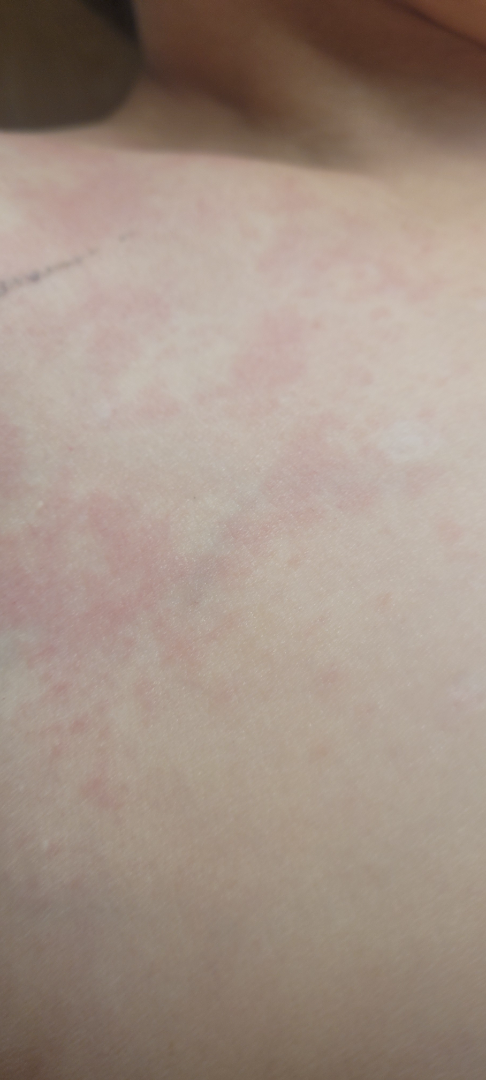assessment — indeterminate from the photograph; shot type — at an angle; anatomic site — head or neck and front of the torso; surface texture — flat; patient's own categorization — a rash; other reported symptoms — none reported; patient — female, age 50–59; present for — less than one week.